A dermoscopic photograph of a skin lesion: 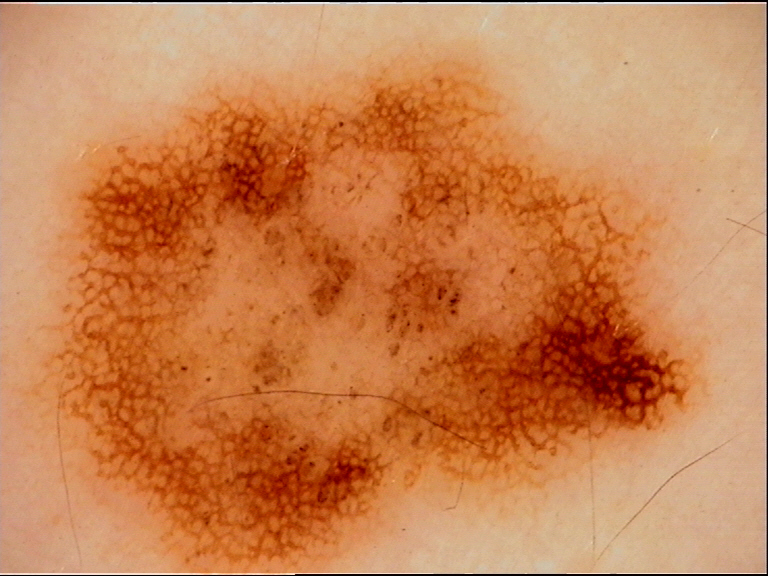Classified as a benign lesion — a dysplastic junctional nevus.